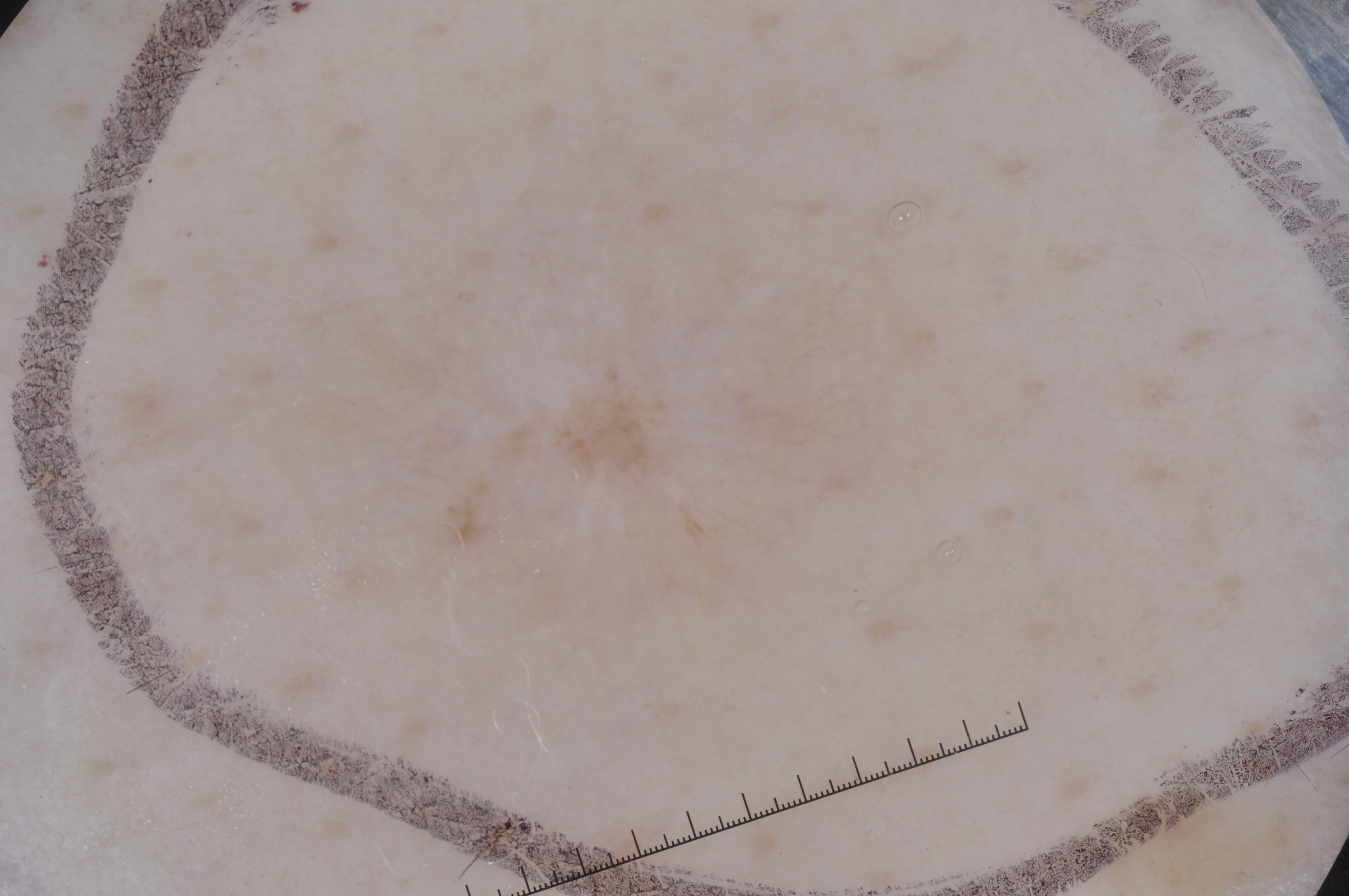  image:
    modality: dermoscopy
  lesion_location:
    bbox_xyxy:
      - 409
      - 298
      - 871
      - 661
  diagnosis:
    name: melanocytic nevus
    malignancy: benign
    lineage: melanocytic
    provenance: clinical